A clinical photograph showing a skin lesion. A female patient in their mid-40s:
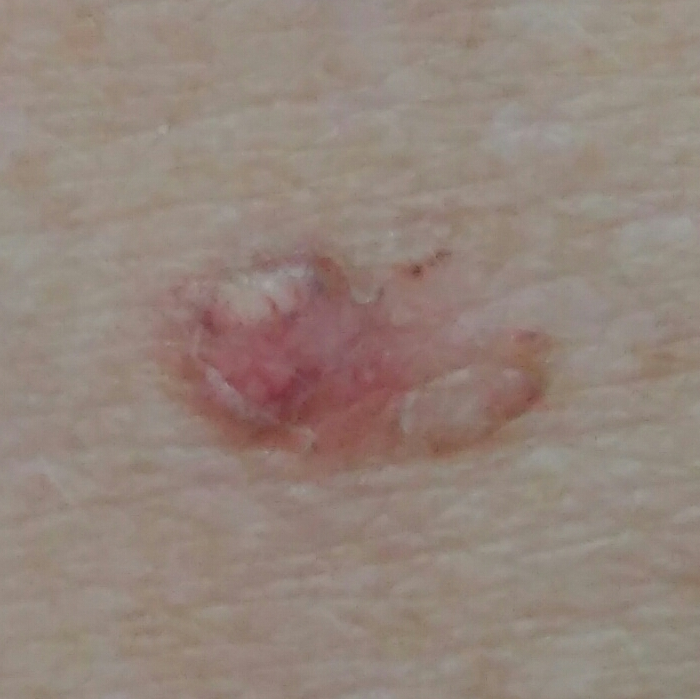Patient and lesion:
The lesion is on the back. The patient reports that the lesion has grown, itches, and is elevated, but has not changed and has not bled.
Diagnosis:
Confirmed on histopathology as a basal cell carcinoma.